This image was taken at a distance. No relevant systemic symptoms. The condition has been present for more than one year. Self-reported Fitzpatrick IV; lay reviewers estimated a Monk skin tone scale of 2. The subject is 50–59, male. The lesion is described as rough or flaky, fluid-filled and raised or bumpy. The back of the hand, leg and top or side of the foot are involved. The patient considered this a rash. The patient indicates burning, enlargement, itching, pain and bleeding.
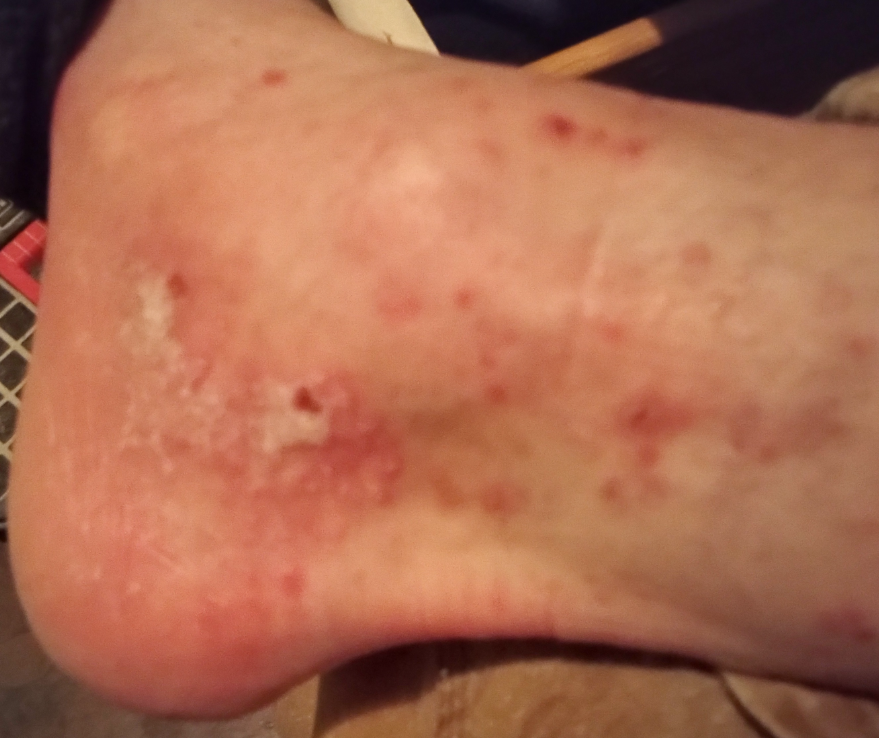<summary>
  <assessment>unable to determine</assessment>
</summary>